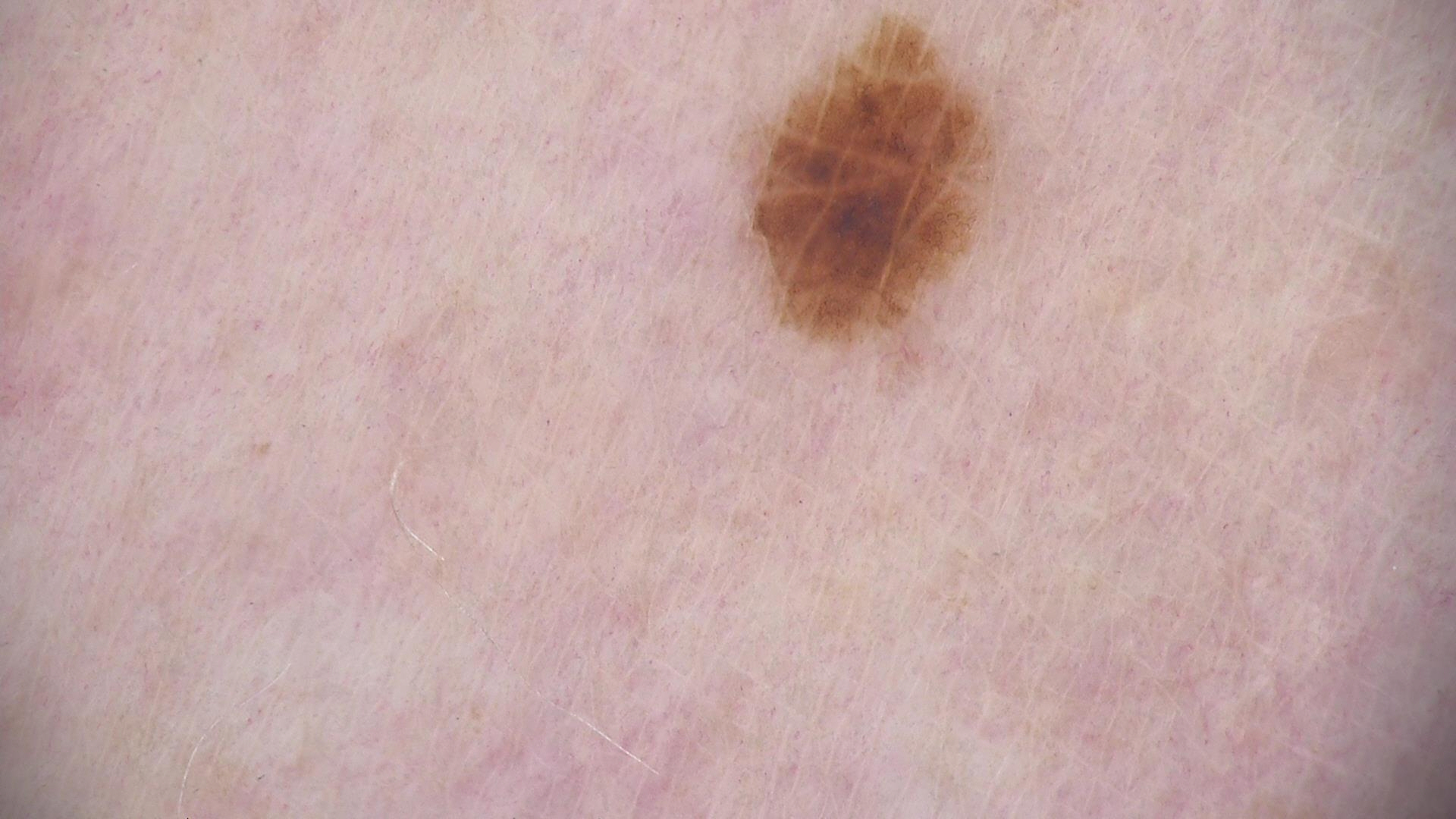The diagnosis was a dysplastic junctional nevus.